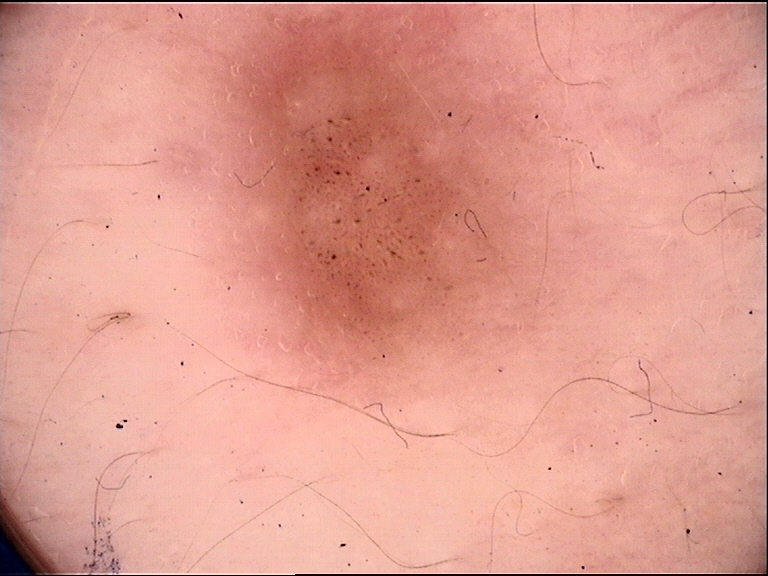The morphology is that of a banal lesion.
Consistent with a compound nevus.